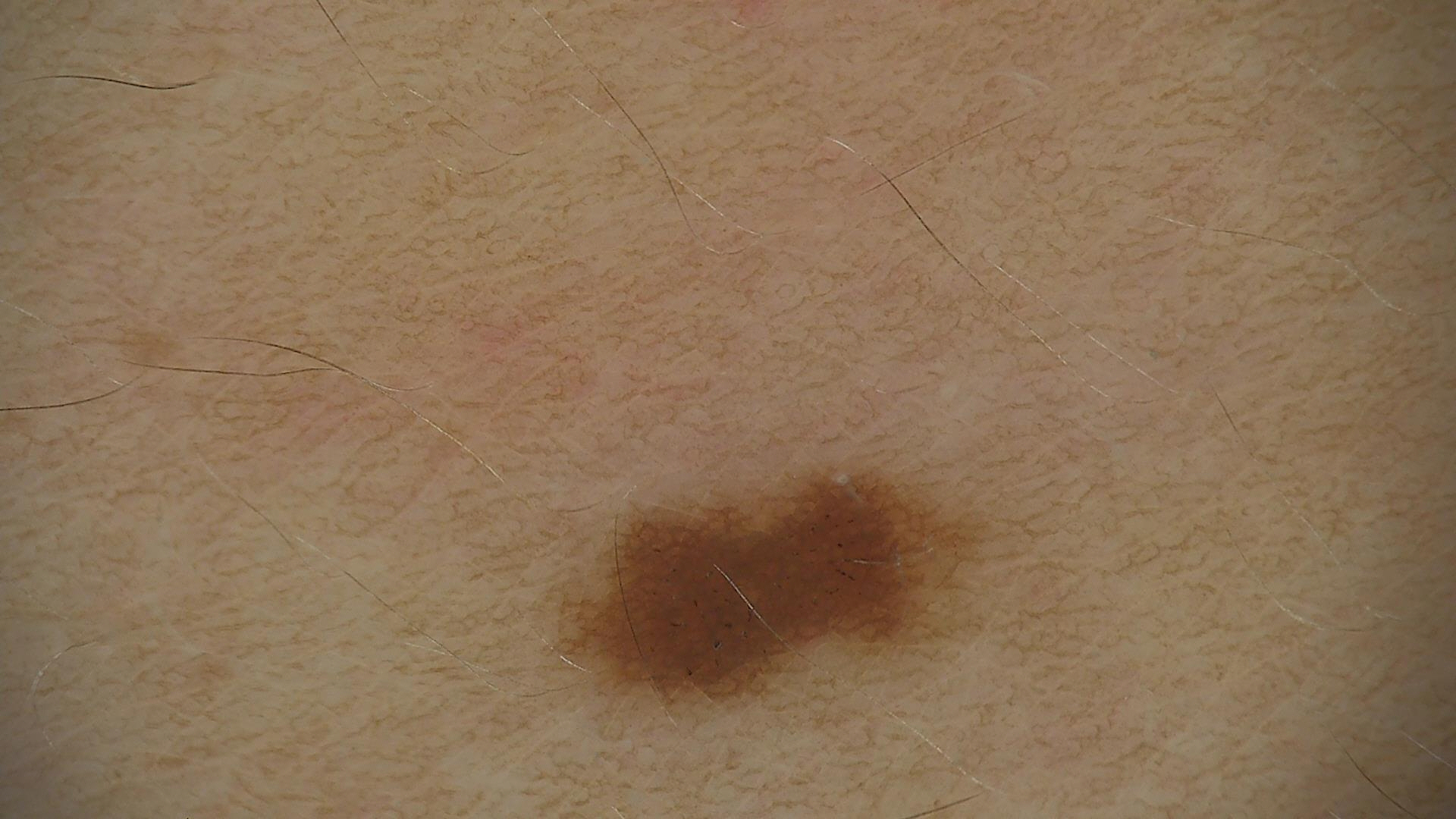A dermoscopic close-up of a skin lesion.
Labeled as a dysplastic junctional nevus.